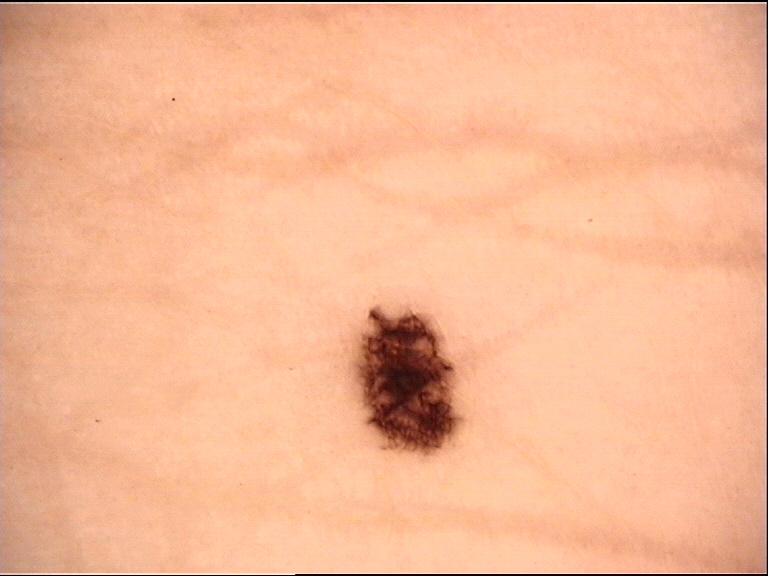imaging: dermoscopy, diagnostic label: acral dysplastic junctional nevus (expert consensus).